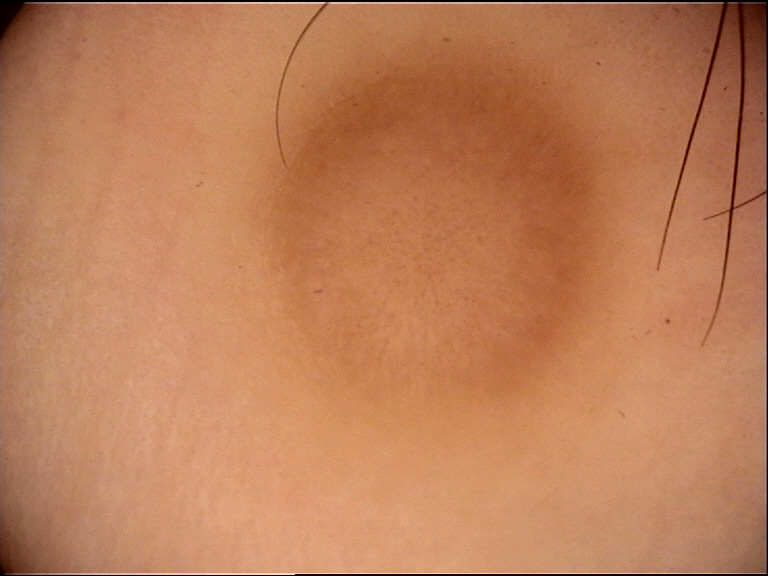A dermatoscopic image of a skin lesion. The diagnosis was a benign lesion — a dermatofibroma.